Dermoscopy of a skin lesion; recorded as skin type II — 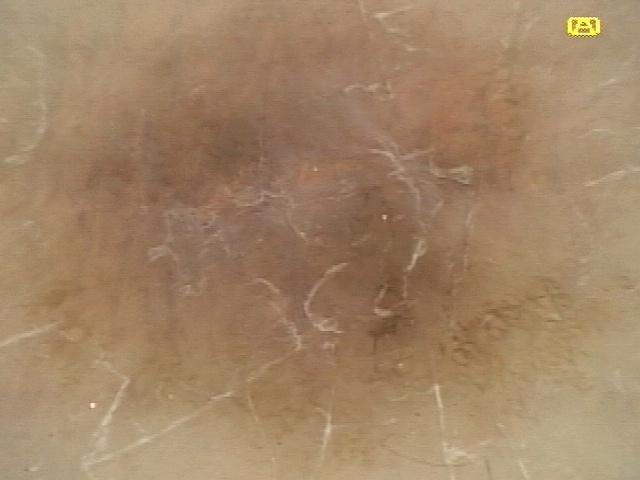anatomic site: a lower extremity | diagnostic label: Dermatofibroma (clinical impression).